A macroscopic clinical photograph of a skin lesion; a female subject 81 years old; collected as part of a research study, without a referral diagnosis.
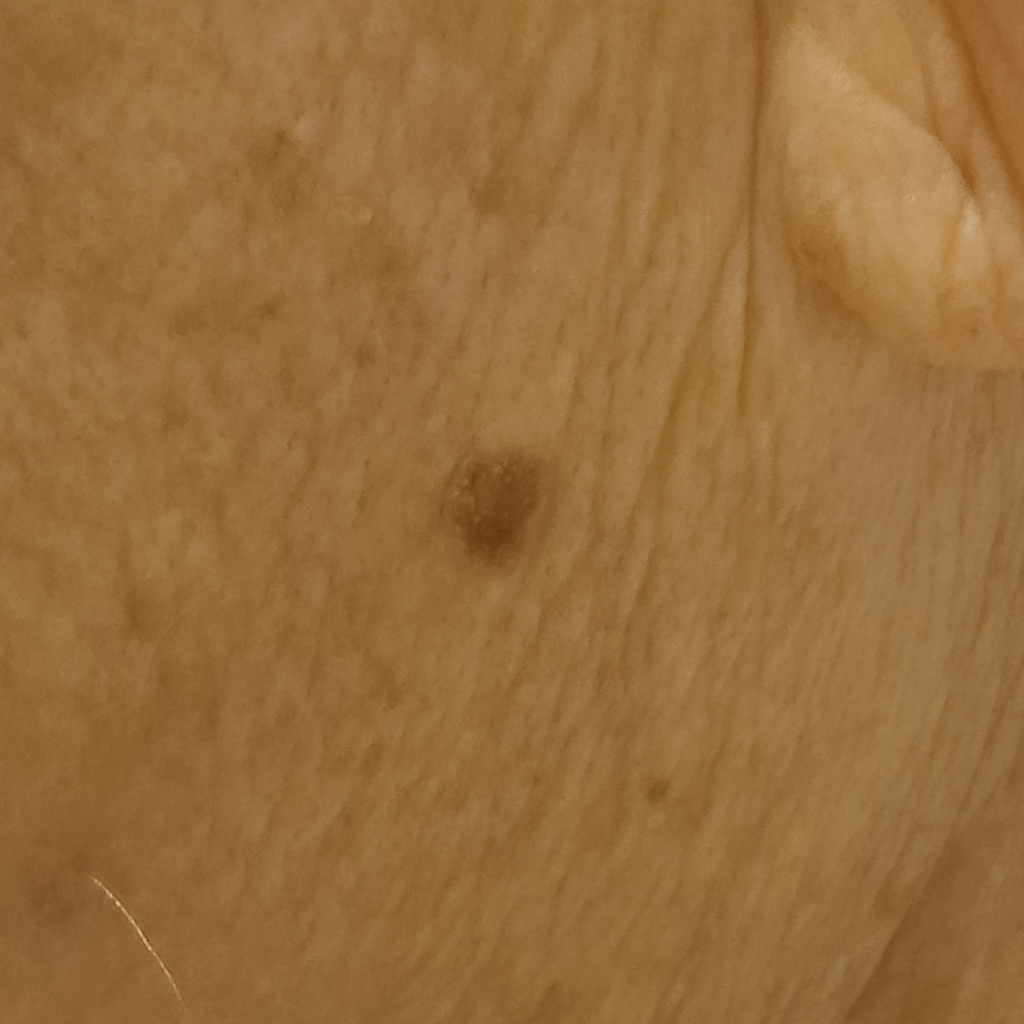Located on the face. Measuring roughly 5.3 mm. Dermatologist review favored a seborrheic keratosis.